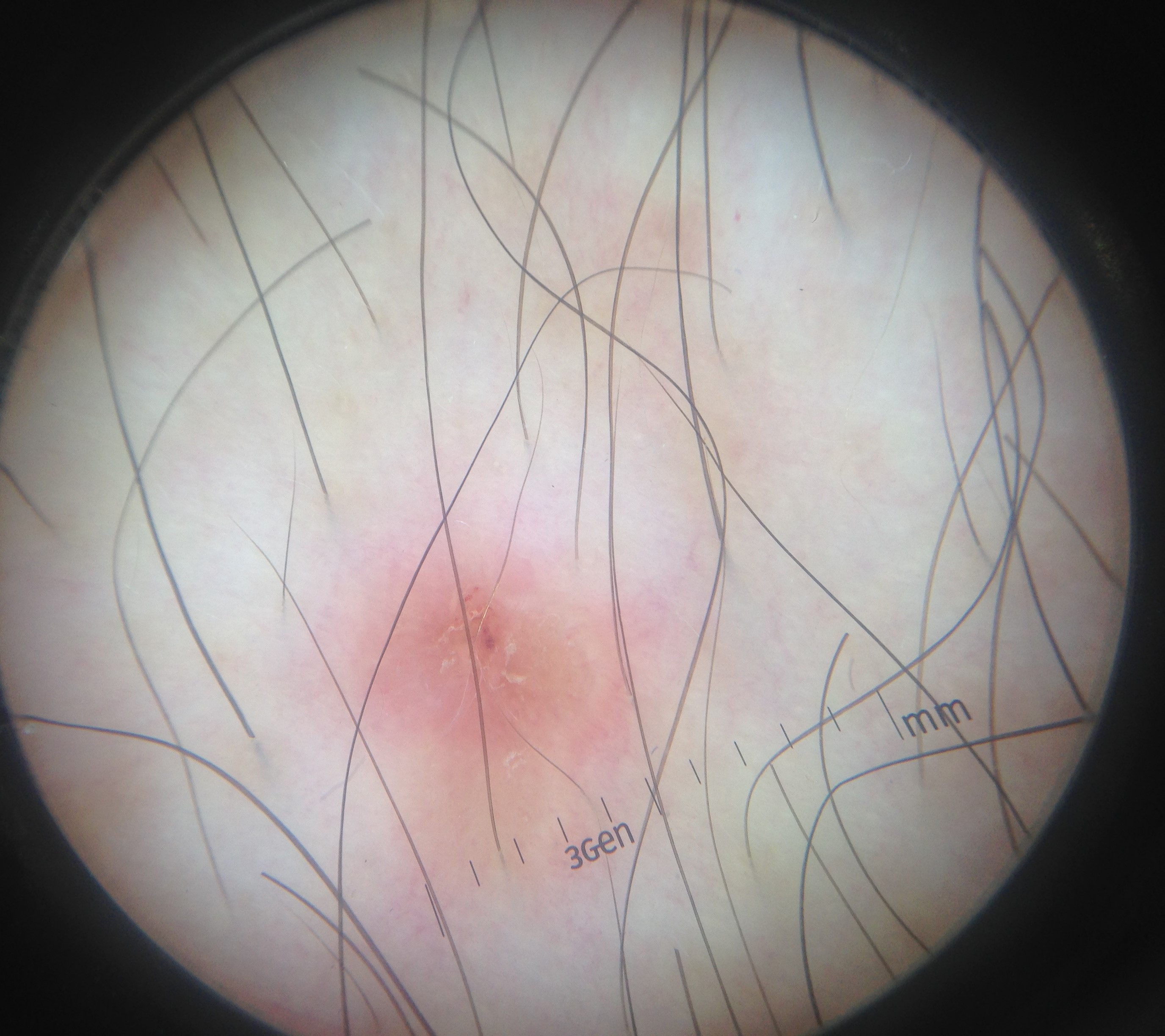Classified as a keratinocytic lesion — a seborrheic keratosis.